A clinical photo of a skin lesion taken with a smartphone · a patient in their mid-70s.
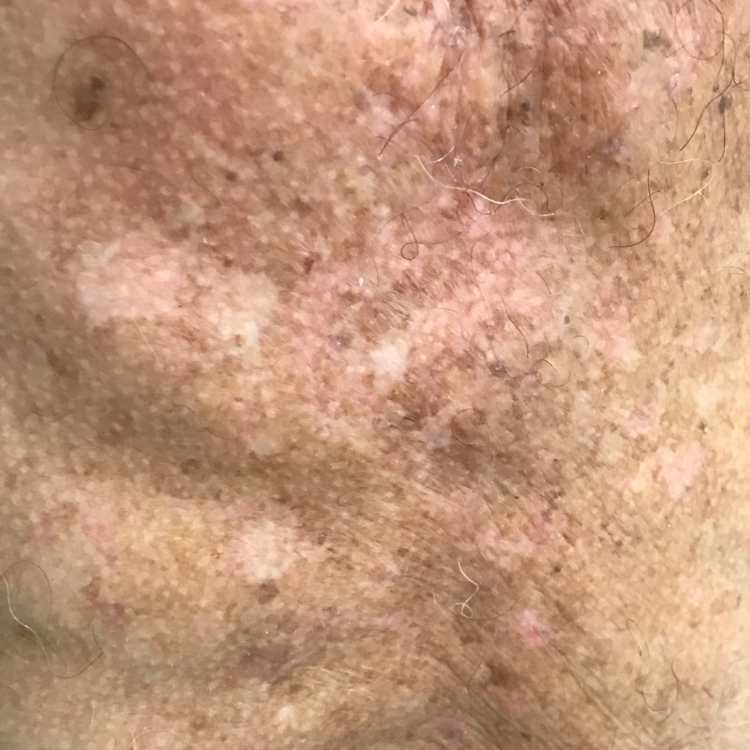{"lesion_location": "the chest", "symptoms": "none reported", "diagnosis": {"name": "actinic keratosis", "code": "ACK", "malignancy": "indeterminate", "confirmation": "clinical consensus"}}